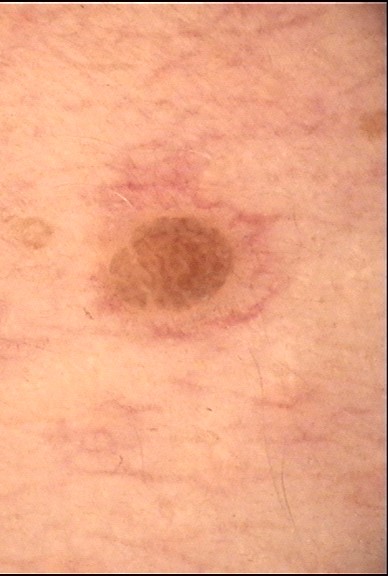Findings:
• lesion type — keratinocytic
• diagnostic label — seborrheic keratosis (expert consensus)